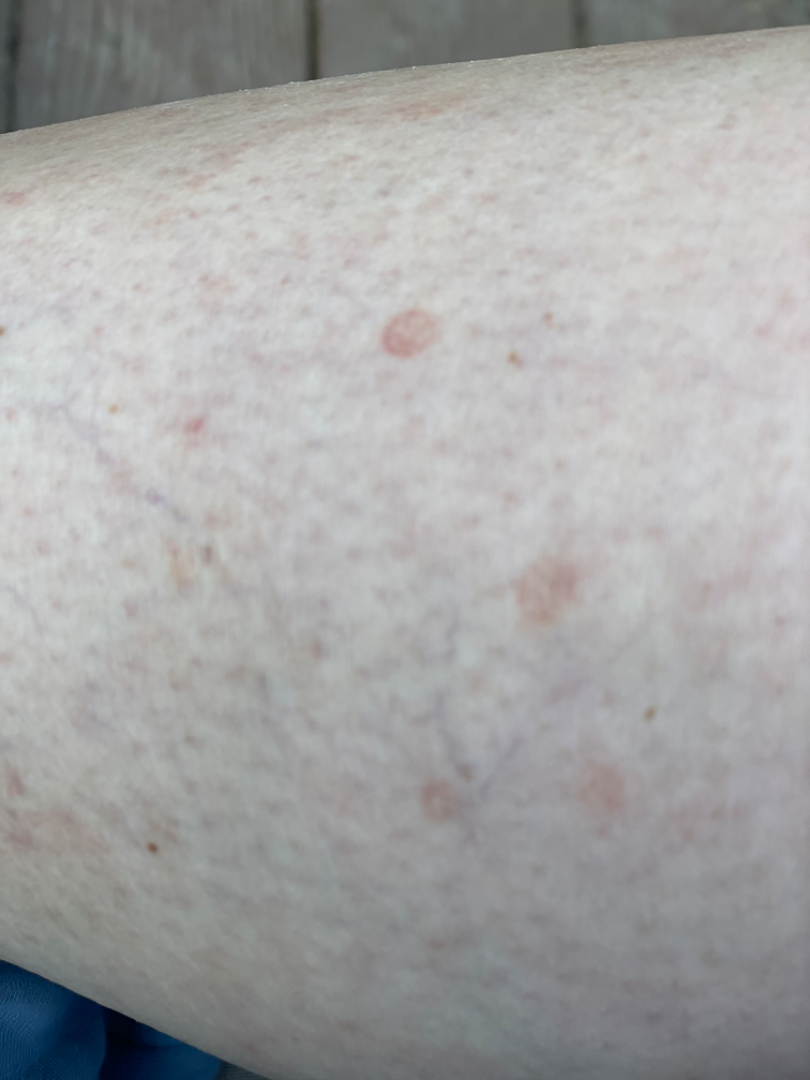The condition could not be reliably identified from the image. Texture is reported as flat. Located on the leg and top or side of the foot. Reported duration is one to four weeks. This is a close-up image. The patient described the issue as a rash.